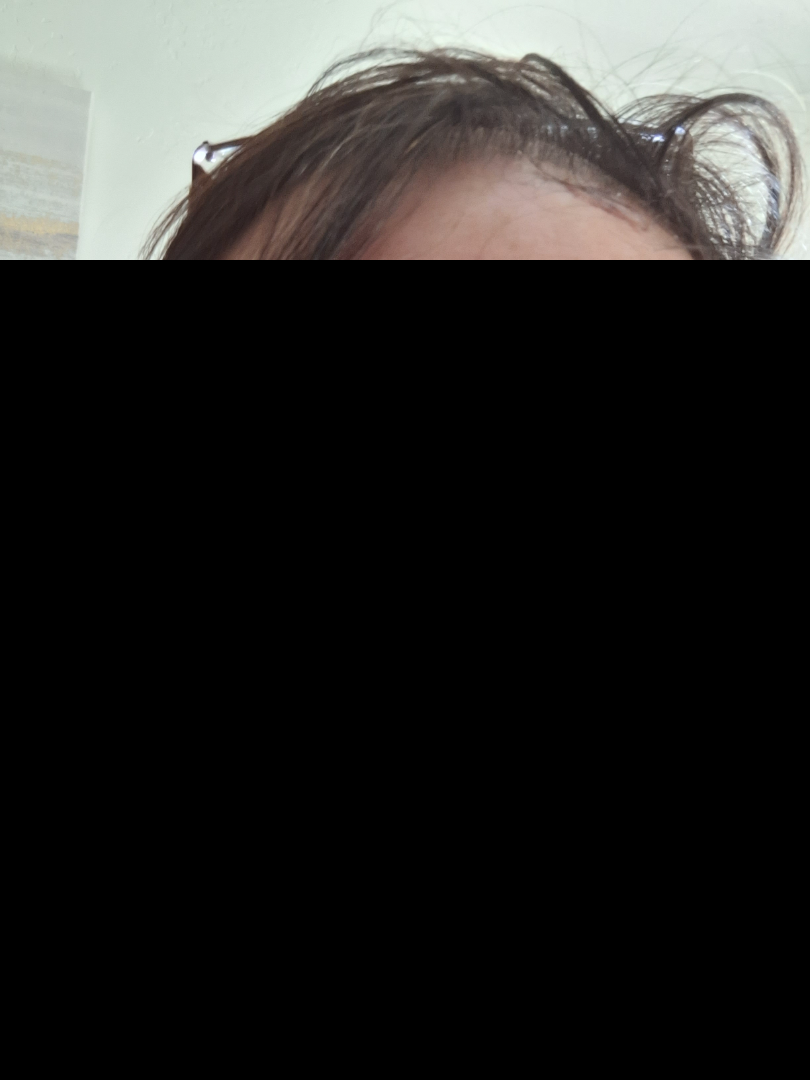Notes:
- differential · the leading consideration is Rosacea; an alternative is Allergic Contact Dermatitis